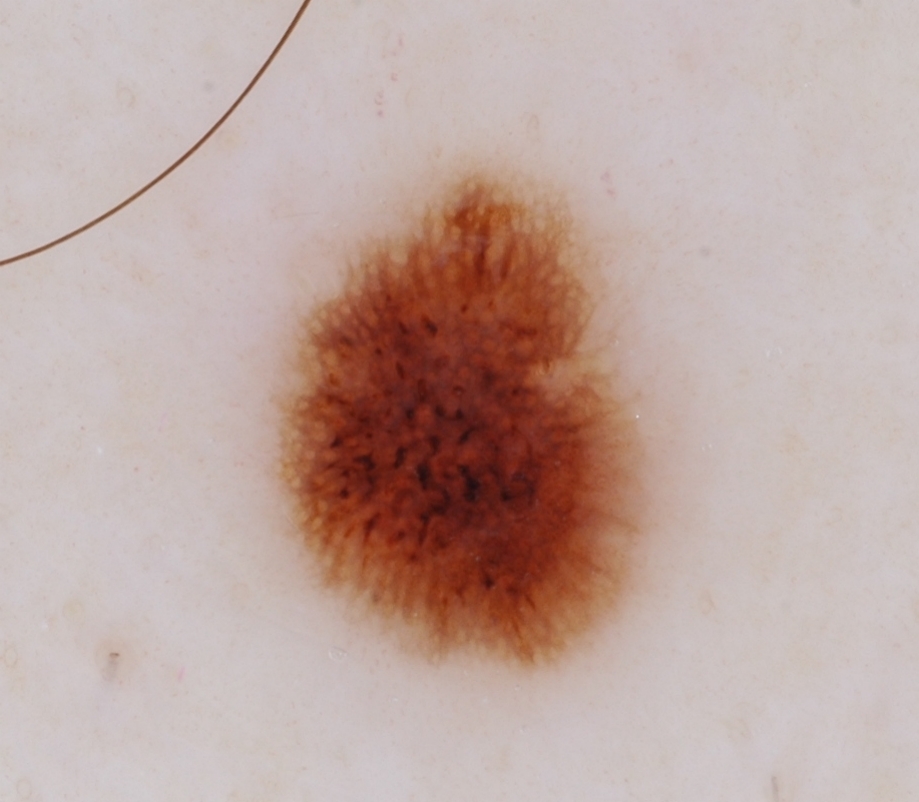image: dermoscopy | location: 264/159/661/673 | lesion extent: ~21% of the field | dermoscopic findings: pigment network and globules | diagnostic label: a melanocytic nevus.